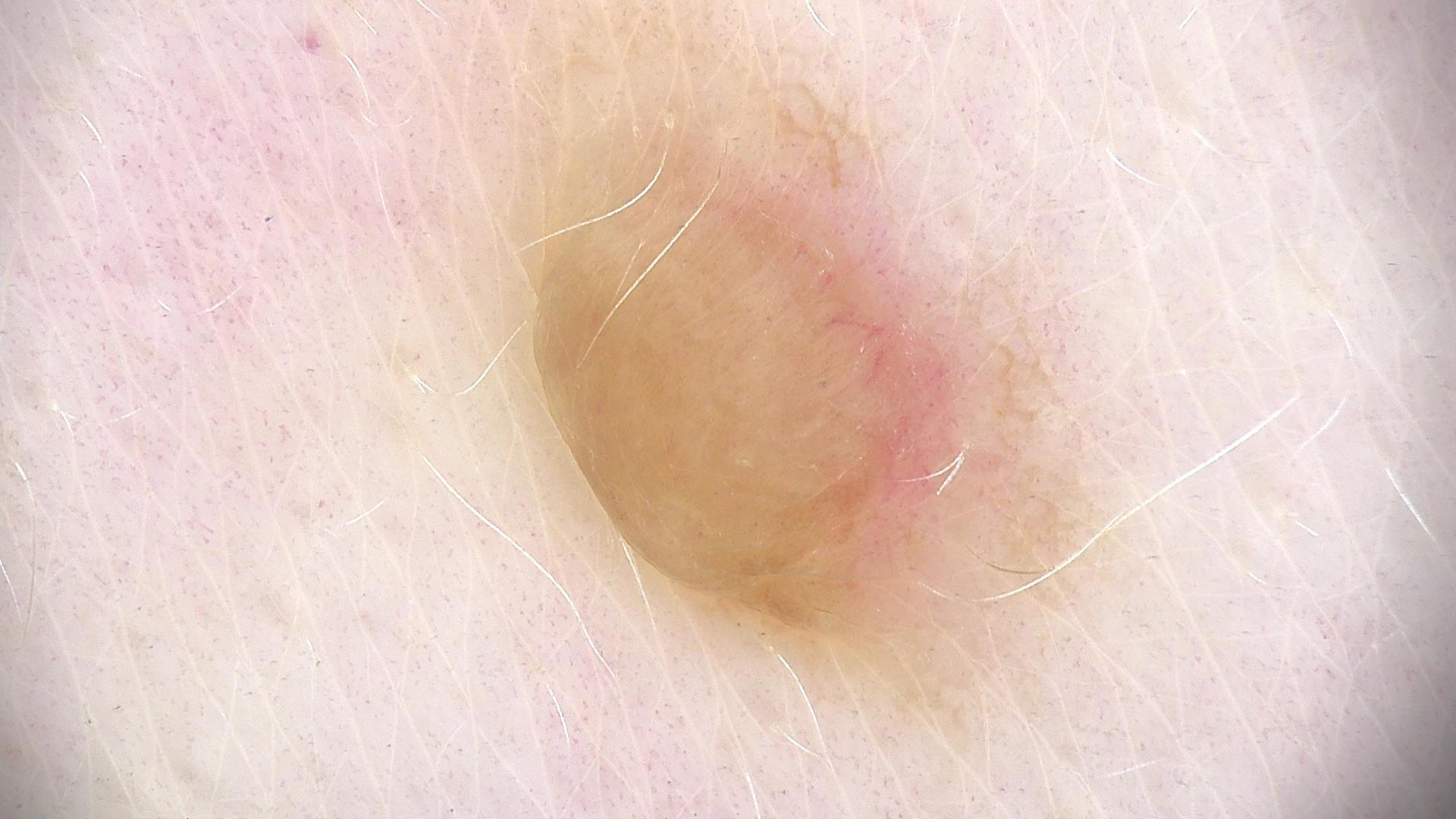The diagnostic label was a dermal nevus.